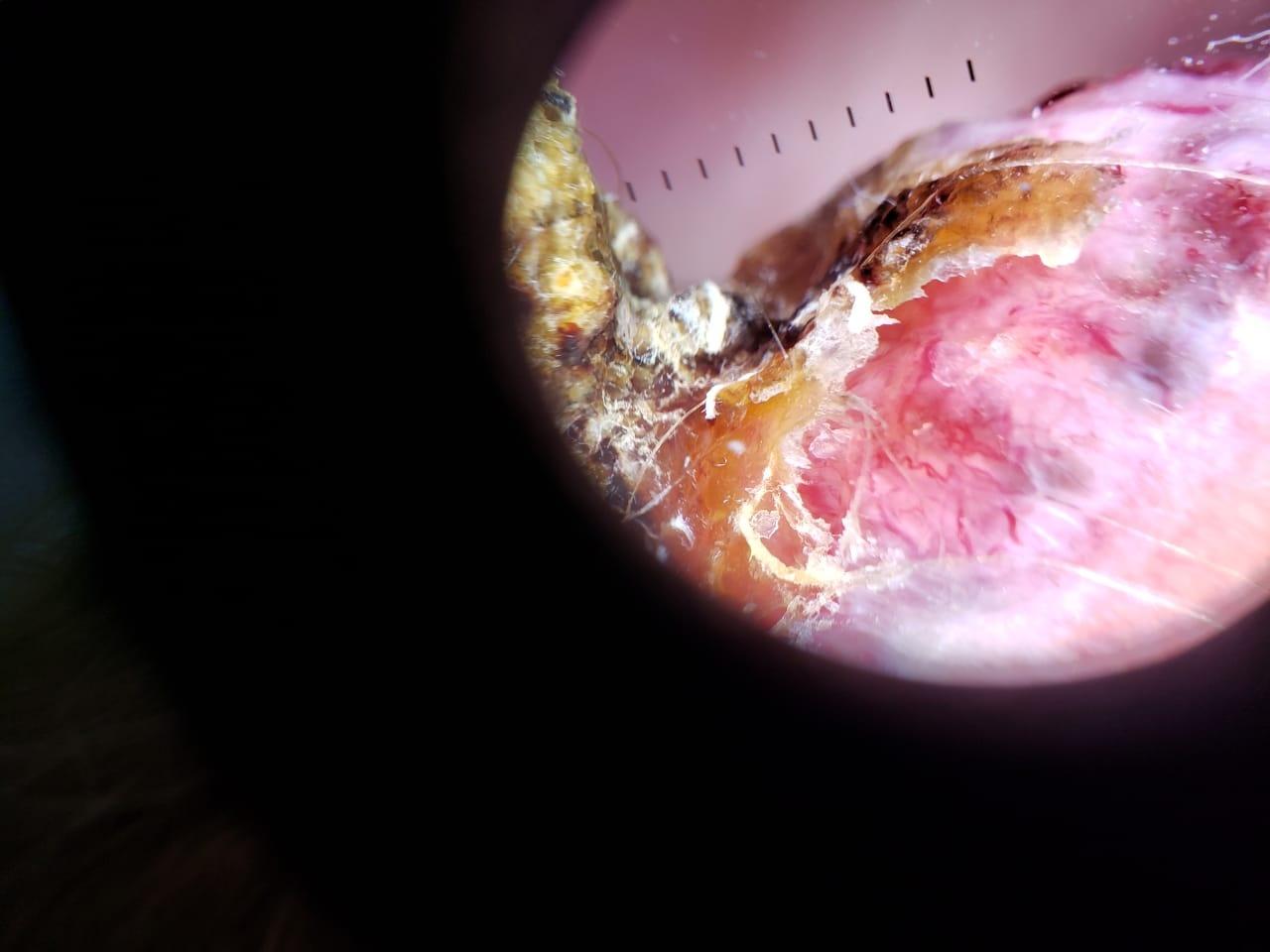diagnosis:
  name: Squamous cell carcinoma
  malignancy: malignant
  confirmation: histopathology
  lineage: epidermal